A male patient age 79. Collected as part of a research study, without a referral diagnosis: 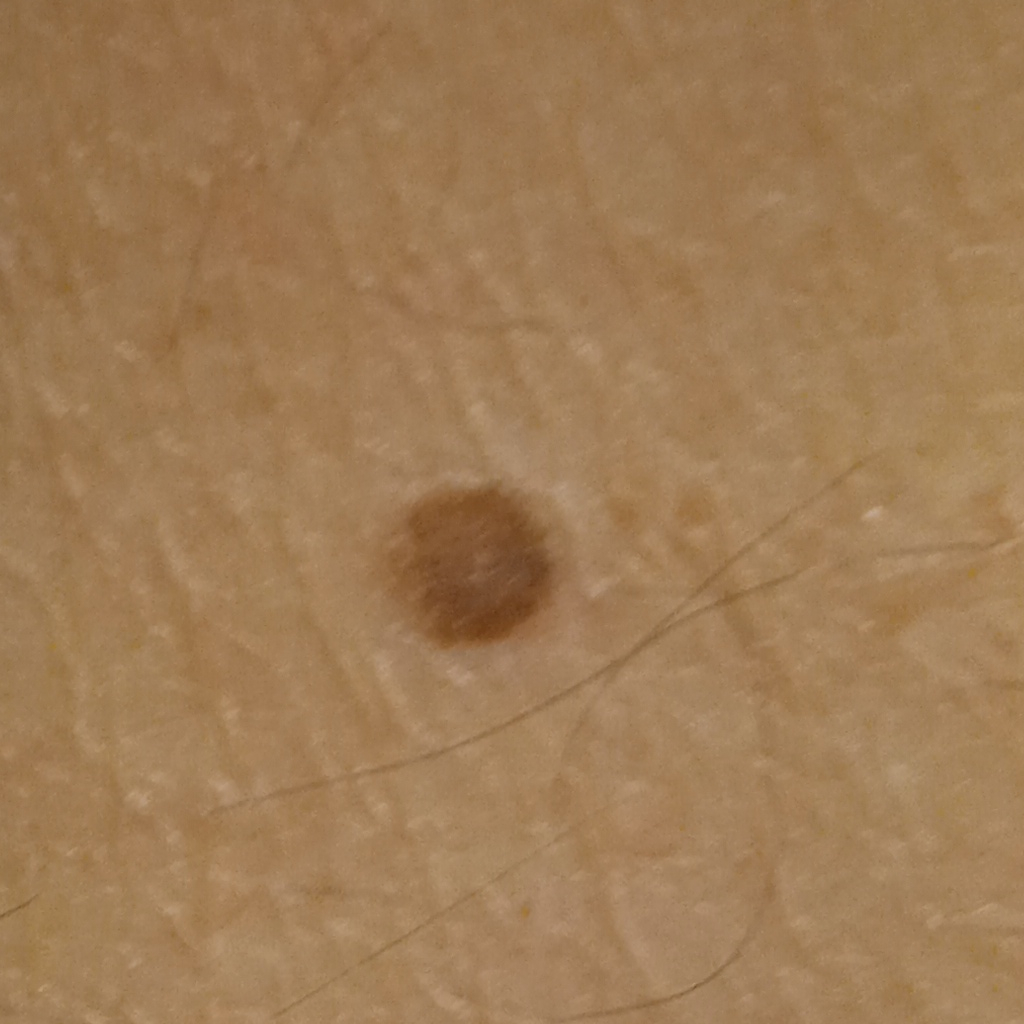Q: Lesion size?
A: 5.8 mm
Q: What was the diagnosis?
A: melanocytic nevus (dermatologist consensus)